Dermoscopy of a skin lesion: 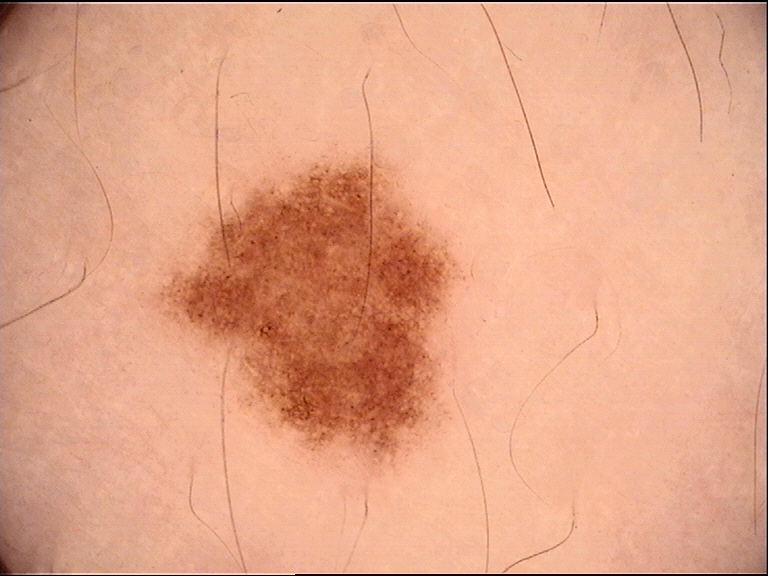The architecture is that of a banal lesion. The diagnosis was a junctional nevus.